The affected area is the head or neck · close-up view: 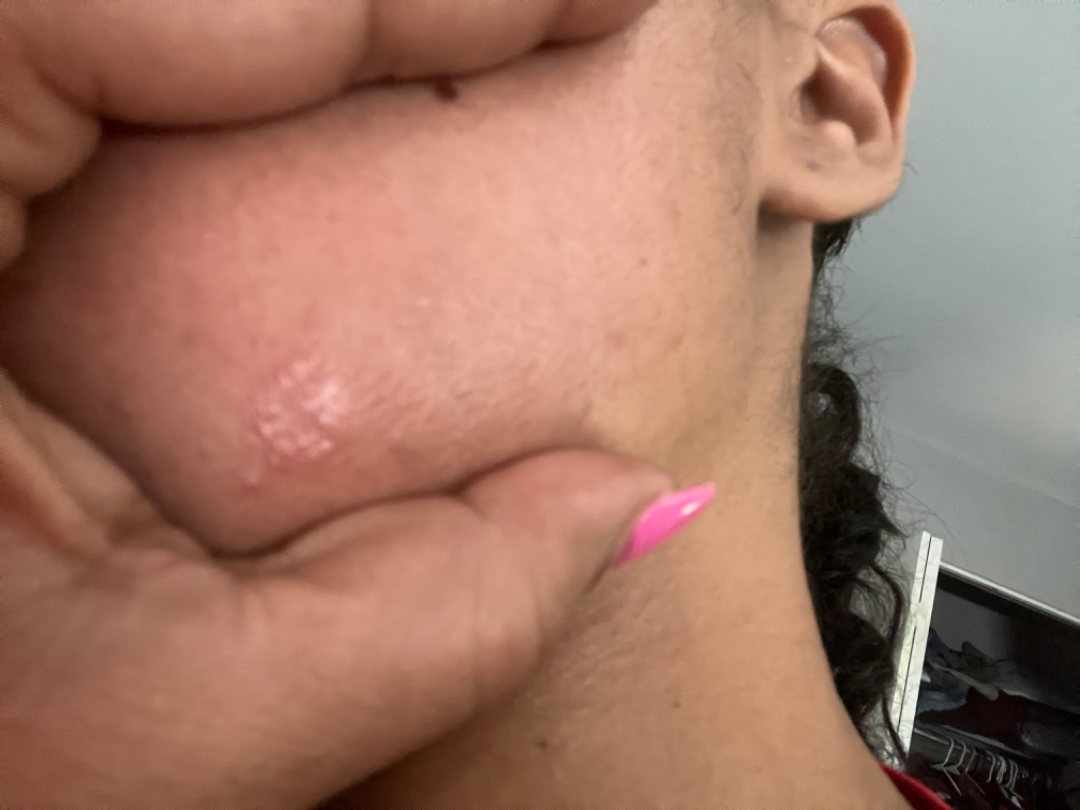The leading consideration is Tinea; also raised was Impetigo; also consider Herpes Simplex.